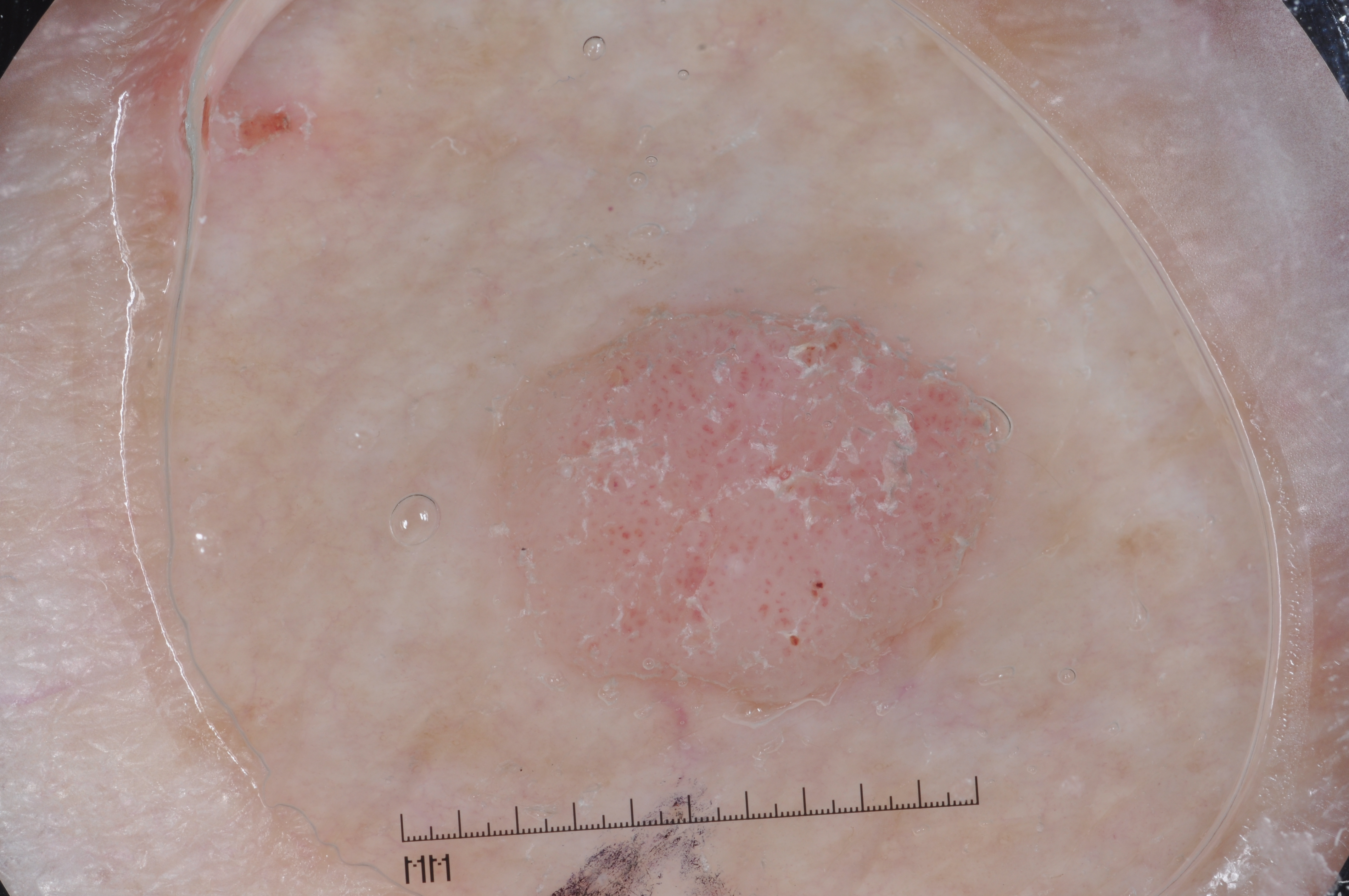Q: What are the patient's age and sex?
A: male, aged 68-72
Q: How was this image acquired?
A: dermoscopy of a skin lesion
Q: What is the lesion's bounding box?
A: left=479, top=272, right=1026, bottom=731
Q: Which dermoscopic features were noted?
A: milia-like cysts
Q: How much of the field does the lesion occupy?
A: moderate
Q: What is this lesion?
A: a seborrheic keratosis, a benign lesion